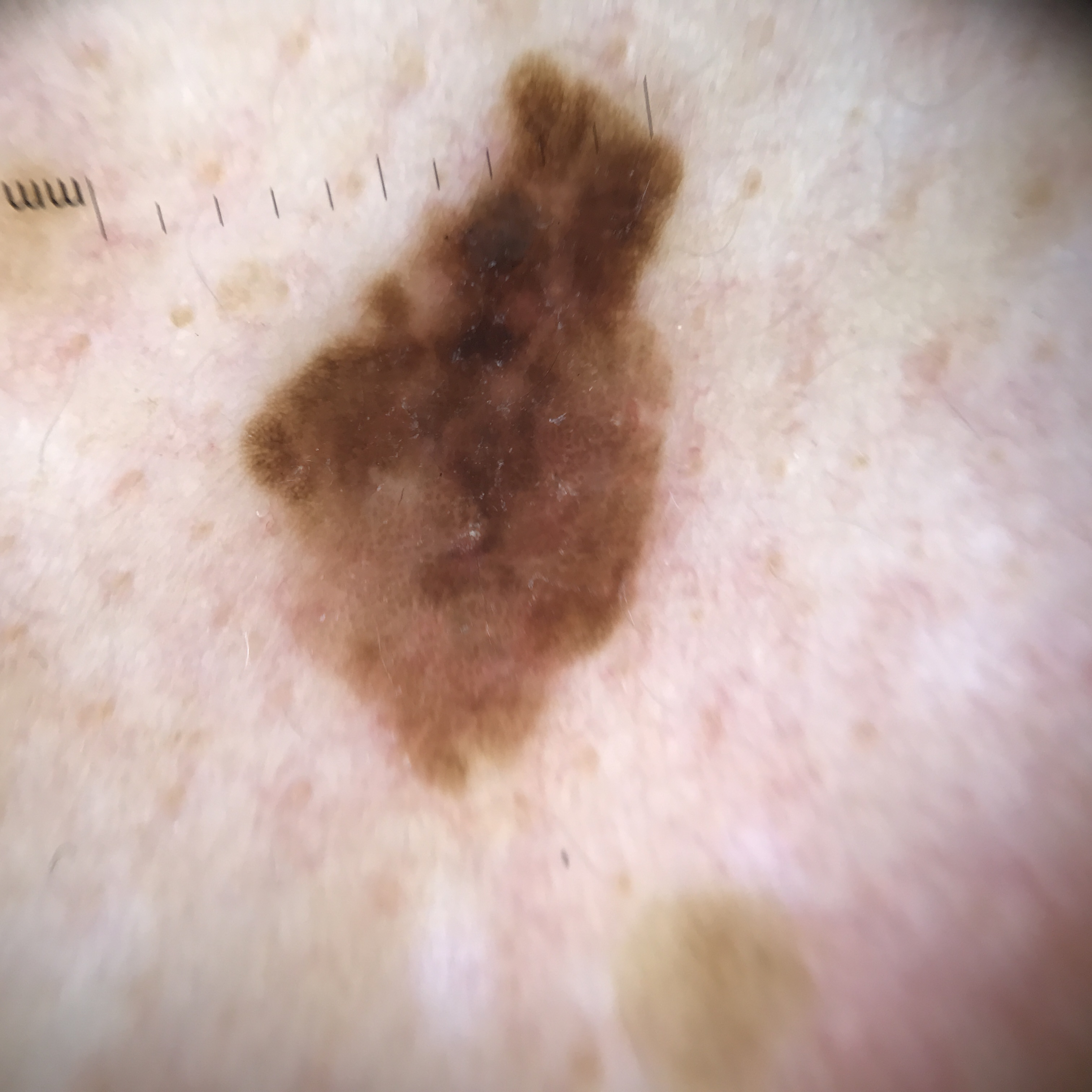A dermoscopic close-up of a skin lesion. Confirmed on histopathology as a melanoma.